A close-up photograph.
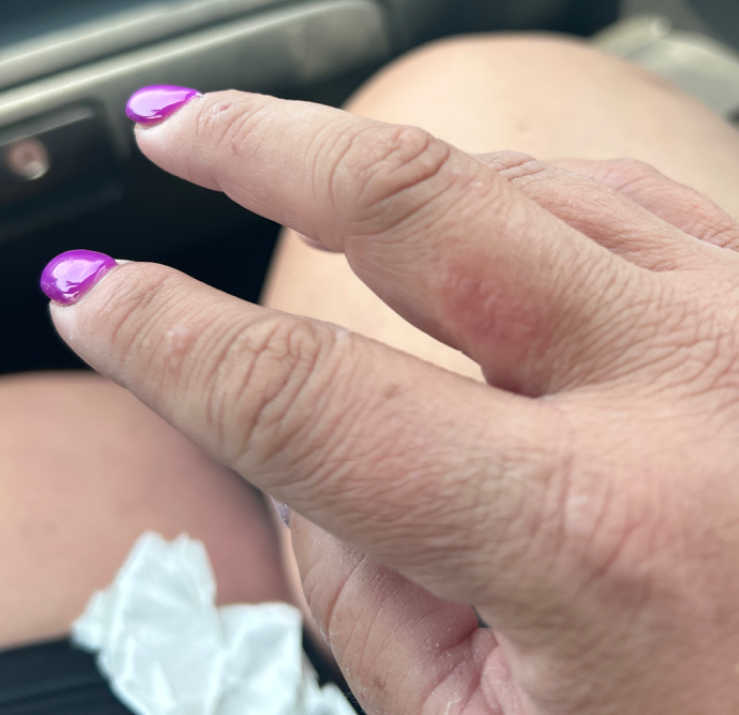Findings: The skin findings could not be characterized from the image.